A clinical close-up photograph of a skin lesion: 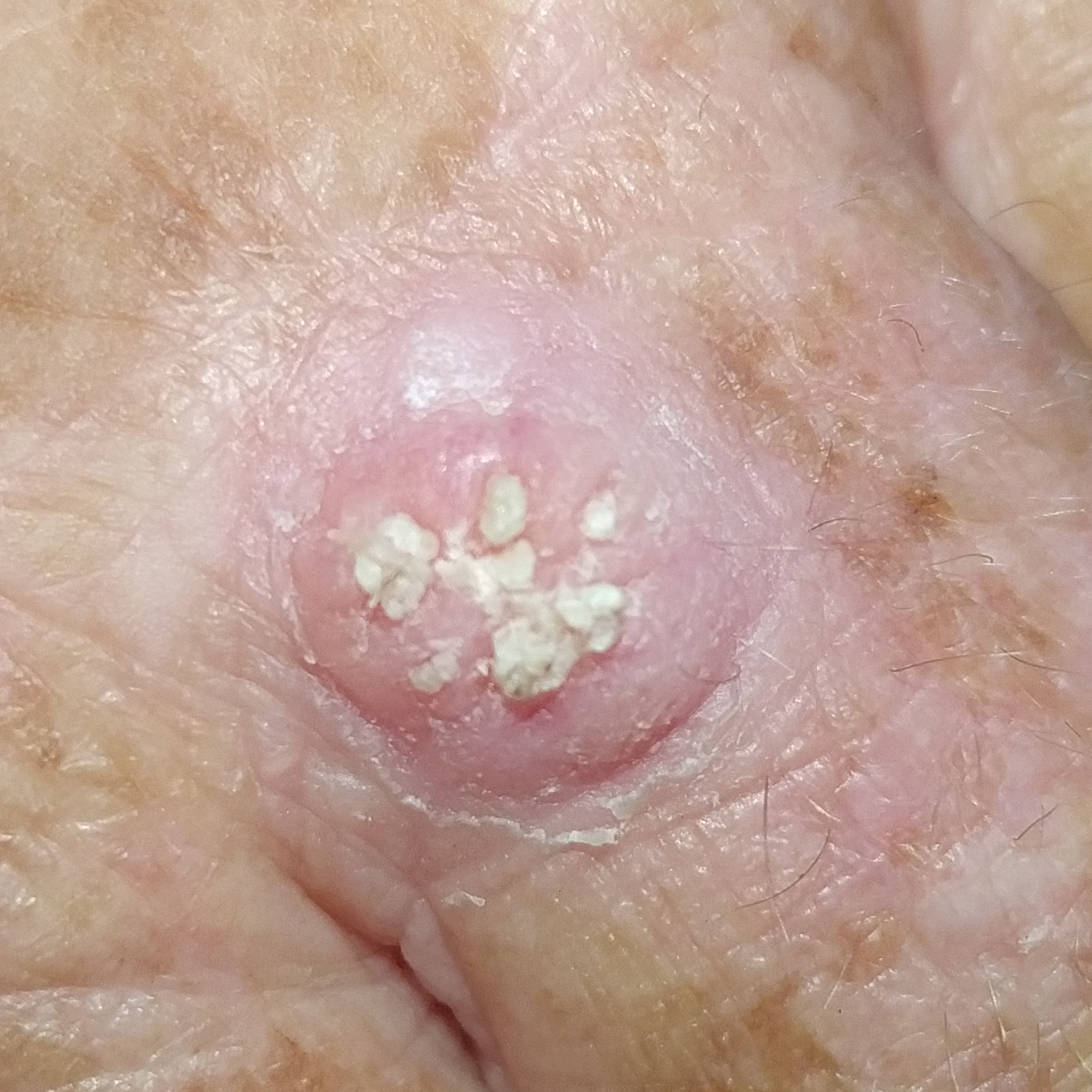diameter: 9x7 mm
reported symptoms: elevation, itching
pathology: squamous cell carcinoma (biopsy-proven)